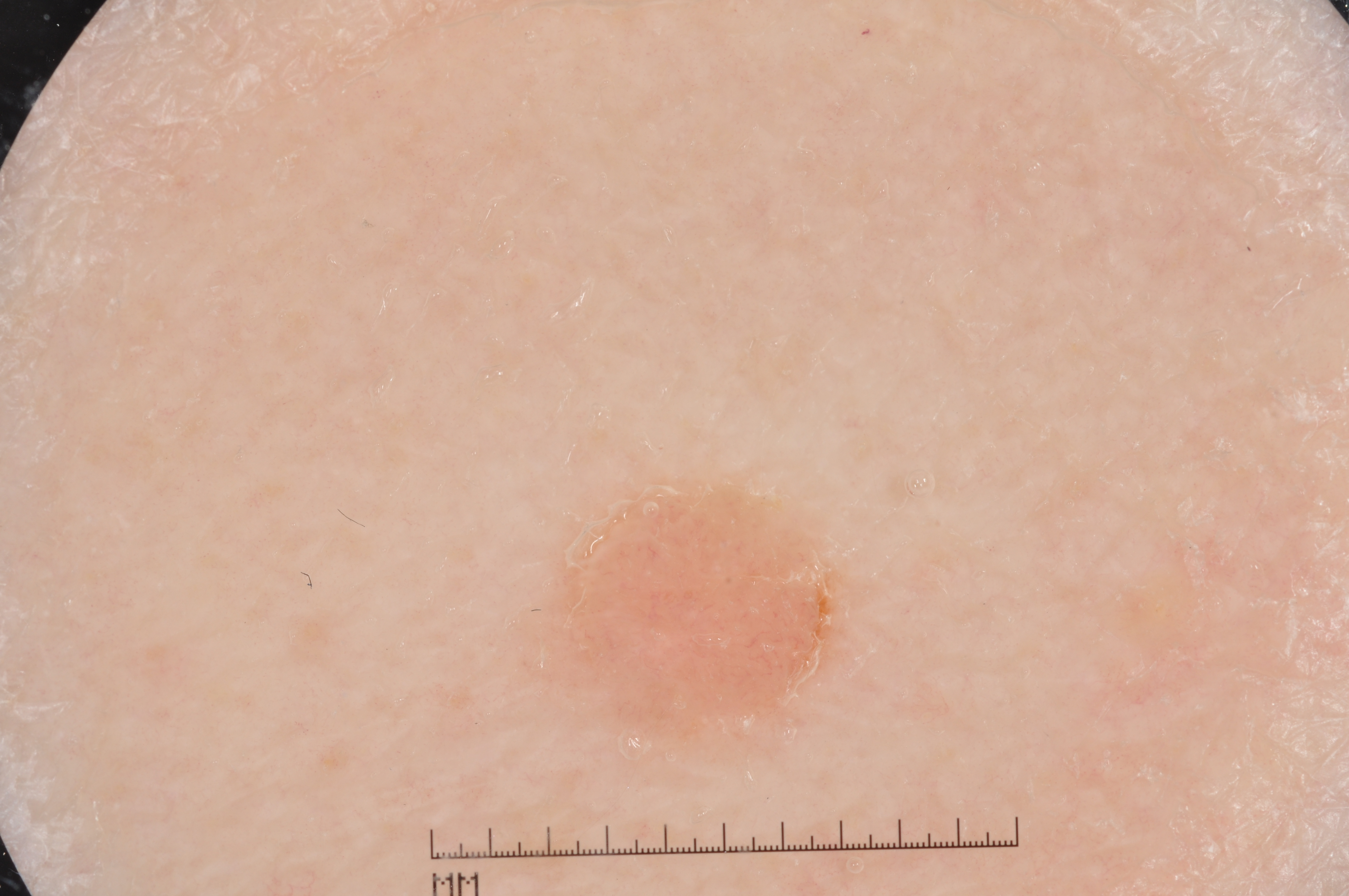{"patient": {"sex": "female", "age_approx": 60}, "image": {"modality": "dermoscopy"}, "lesion_extent": {"approx_field_fraction_pct": 5}, "lesion_location": {"bbox_xyxy": [548, 483, 843, 742]}, "dermoscopic_features": {"present": ["milia-like cysts"], "absent": ["pigment network", "negative network", "streaks"]}, "diagnosis": {"name": "melanocytic nevus", "malignancy": "benign", "lineage": "melanocytic", "provenance": "clinical"}}